The patient is a female aged 60–69; the lesion involves the head or neck; close-up view — 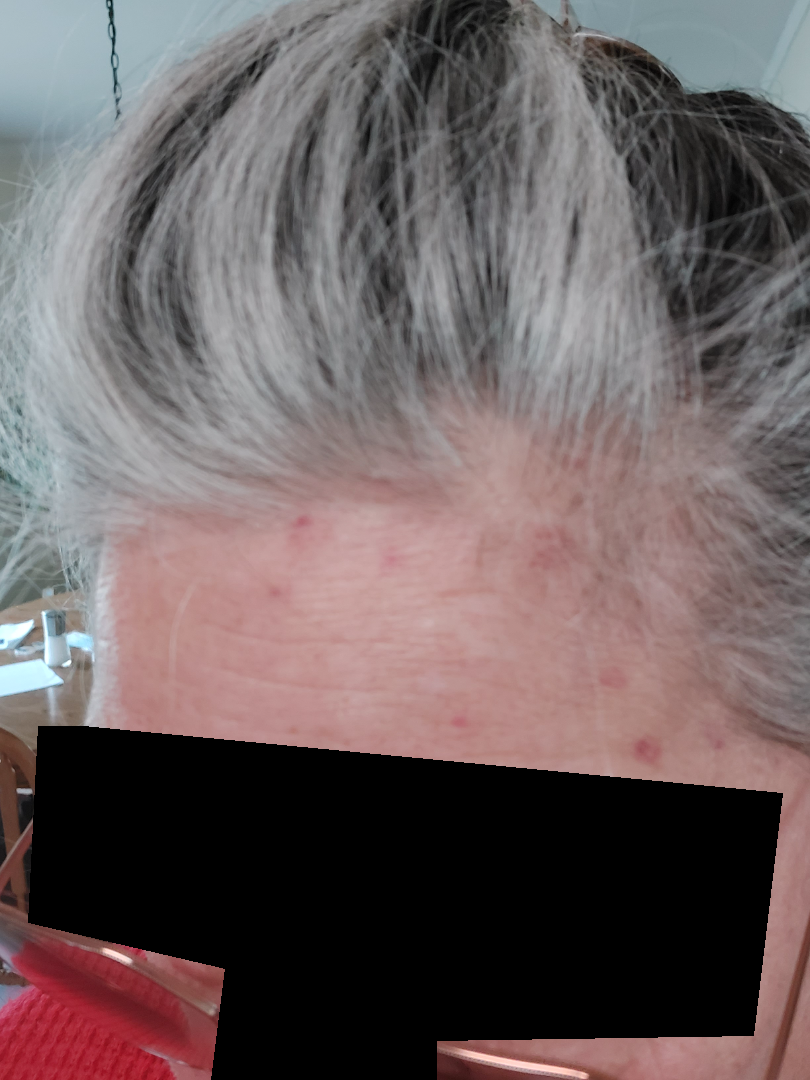Assessment: The skin findings could not be characterized from the image. Clinical context: The patient reports the condition has been present for about one day. Texture is reported as flat. Symptoms reported: bothersome appearance. Self-categorized by the patient as skin that appeared healthy to them.